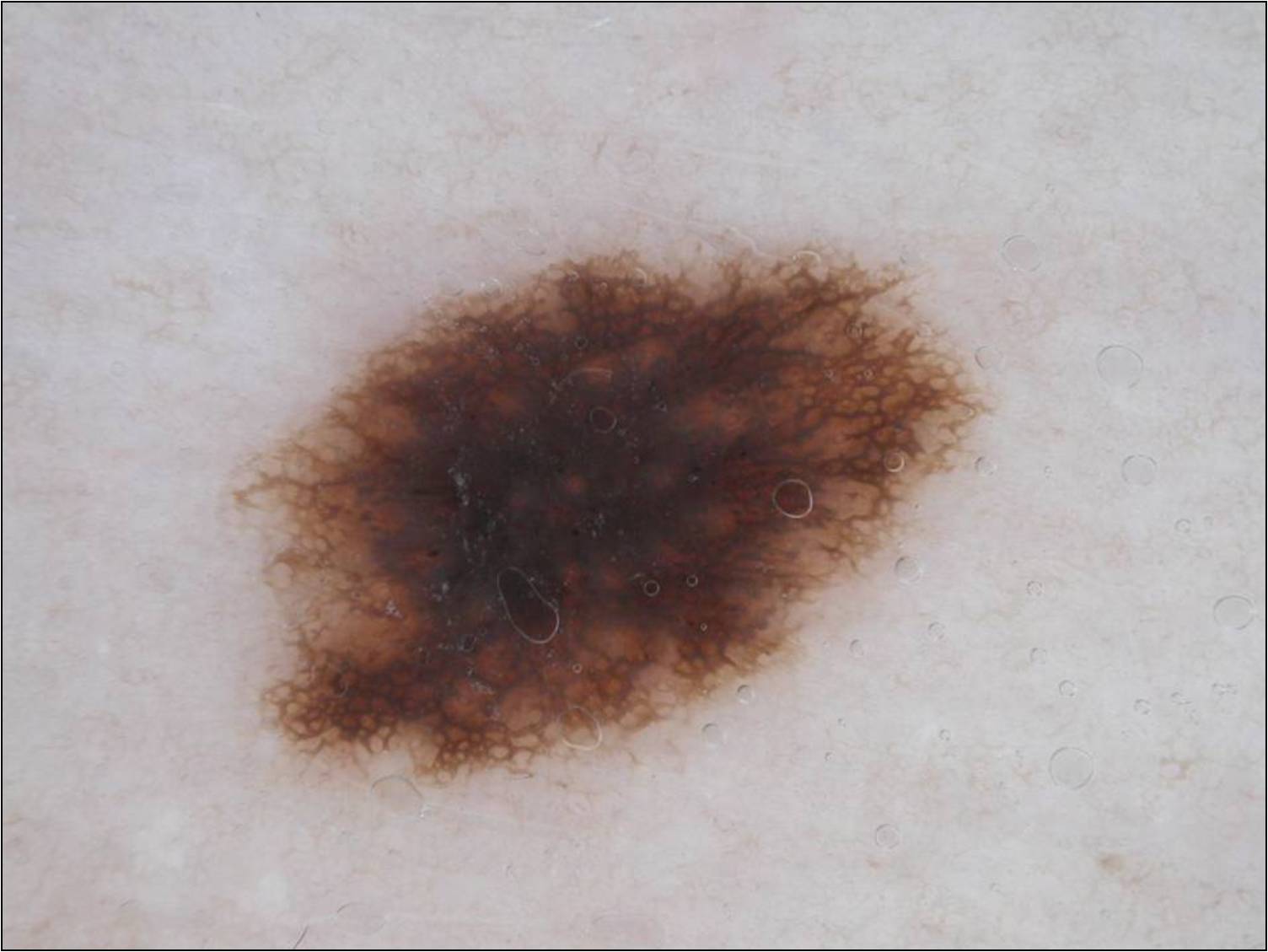patient=male, about 60 years old
imaging=dermoscopy
lesion size=~24% of the field
location=234, 234, 981, 786
dermoscopic pattern=globules and pigment network
impression=a melanocytic nevus, a benign skin lesion